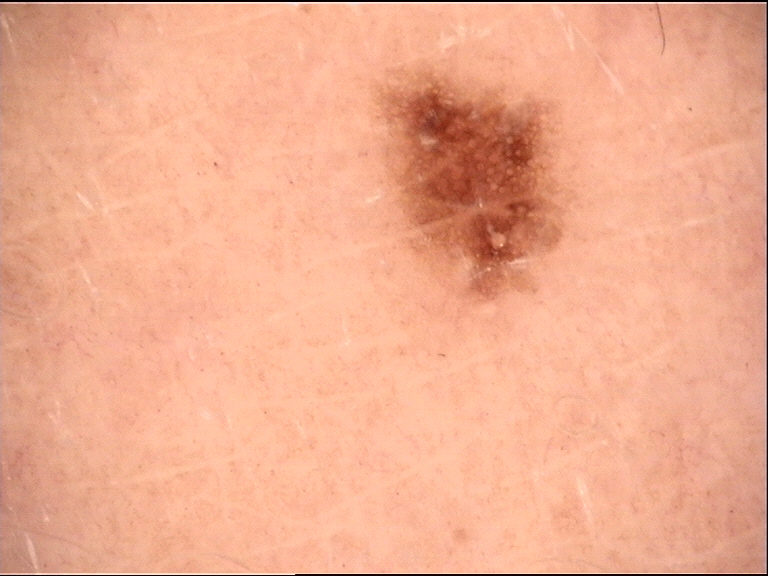Case:
– diagnosis · dysplastic junctional nevus (expert consensus)